A dermoscopic close-up of a skin lesion. The chart documents a previous melanoma. A male subject about 60 years old — 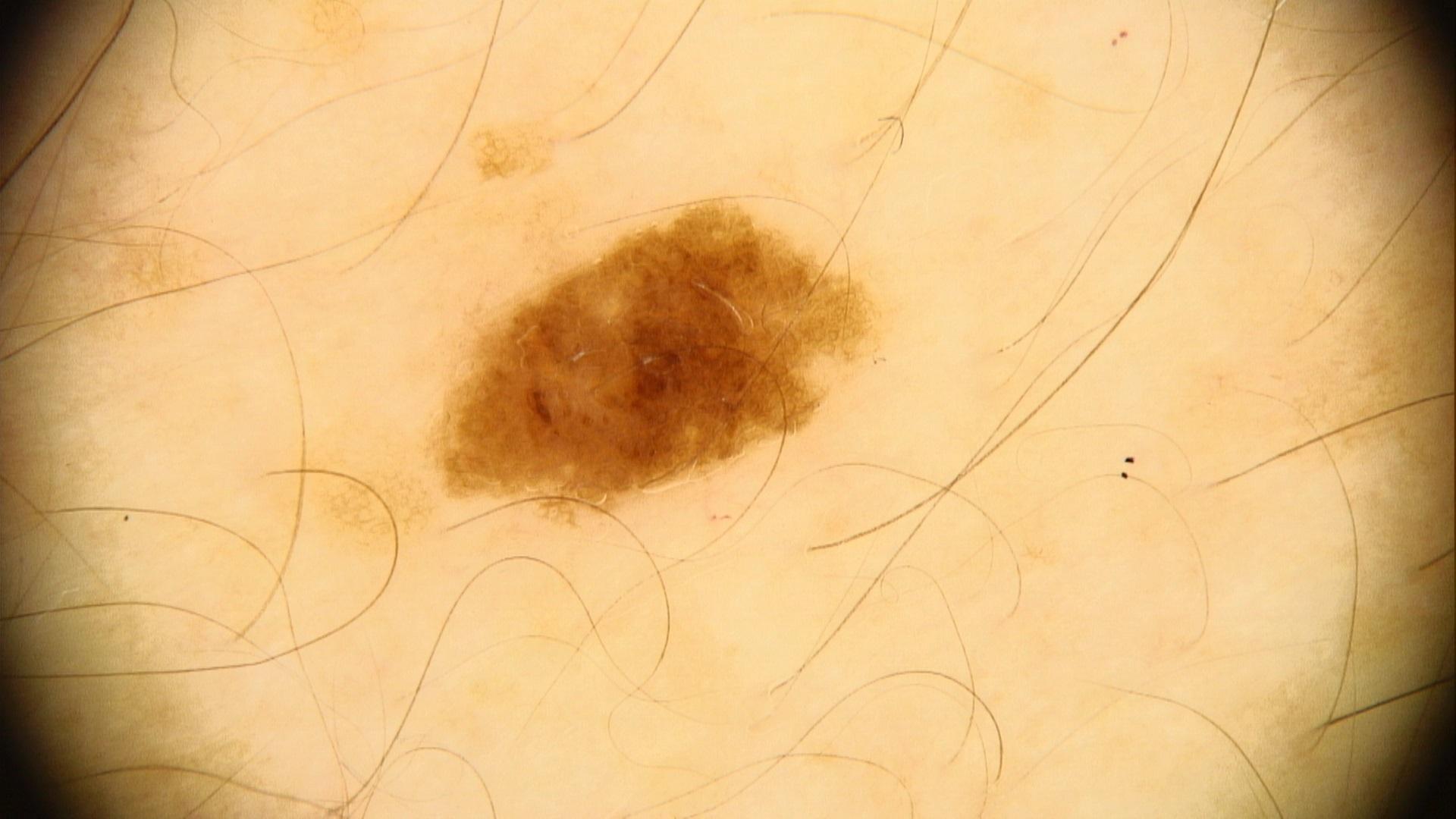{
  "lesion_location": {
    "region": "the trunk"
  },
  "diagnosis": {
    "name": "Nevus",
    "malignancy": "benign",
    "confirmation": "expert clinical impression",
    "lineage": "melanocytic"
  }
}